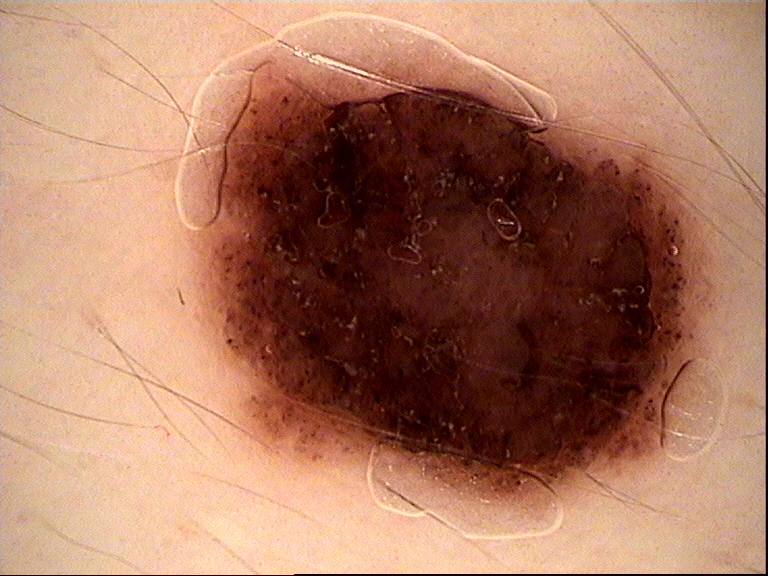{"image": "dermoscopy", "diagnosis": {"name": "compound nevus", "code": "cb", "malignancy": "benign", "super_class": "melanocytic", "confirmation": "expert consensus"}}